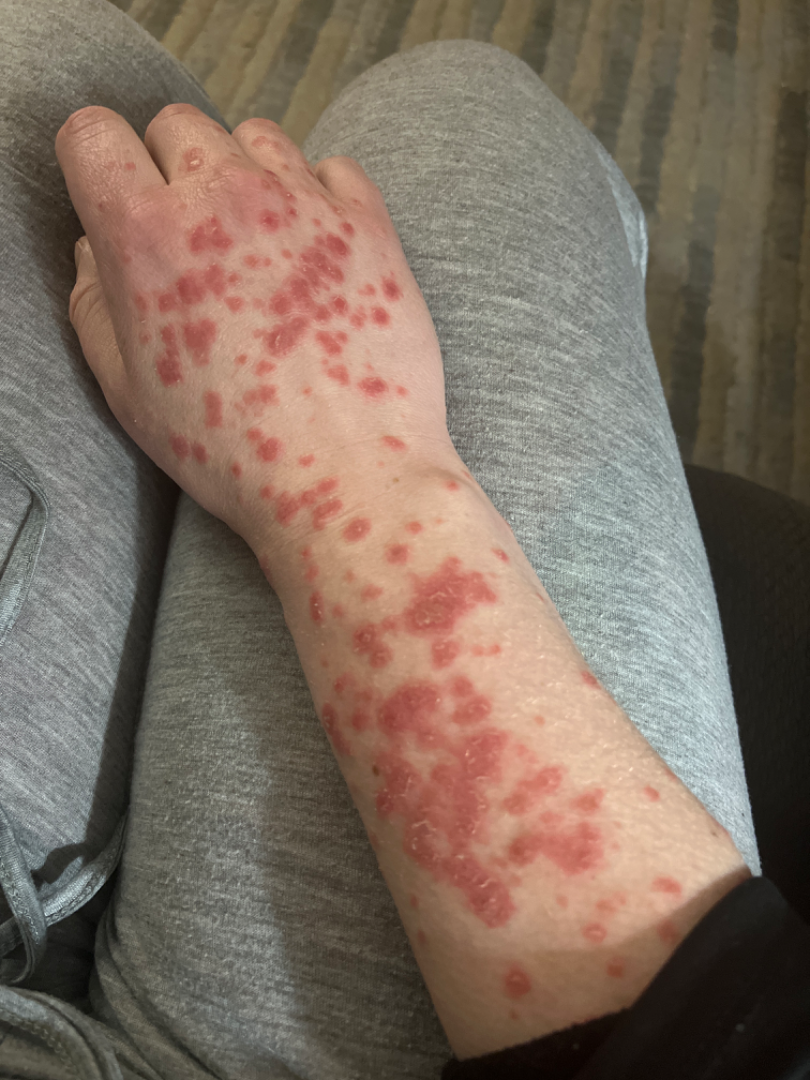The photo was captured at a distance. Fitzpatrick III; human graders estimated MST 2. On teledermatology review: Erythema multiforme (primary).